Close-up view.
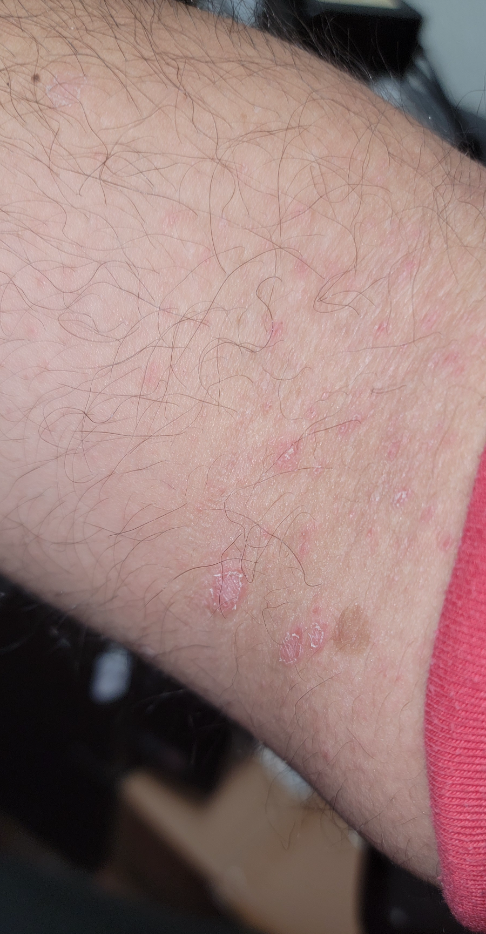assessment — the differential, in no particular order, includes Tinea and Pityriasis rosea; less probable is Psoriasis